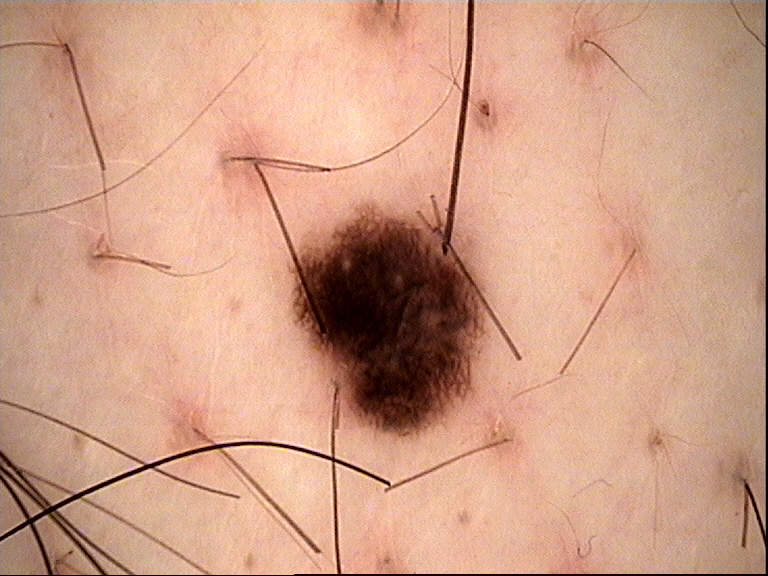diagnosis = dysplastic junctional nevus (expert consensus).